The patient describes having few moles overall; the patient says their skin tans without first burning:
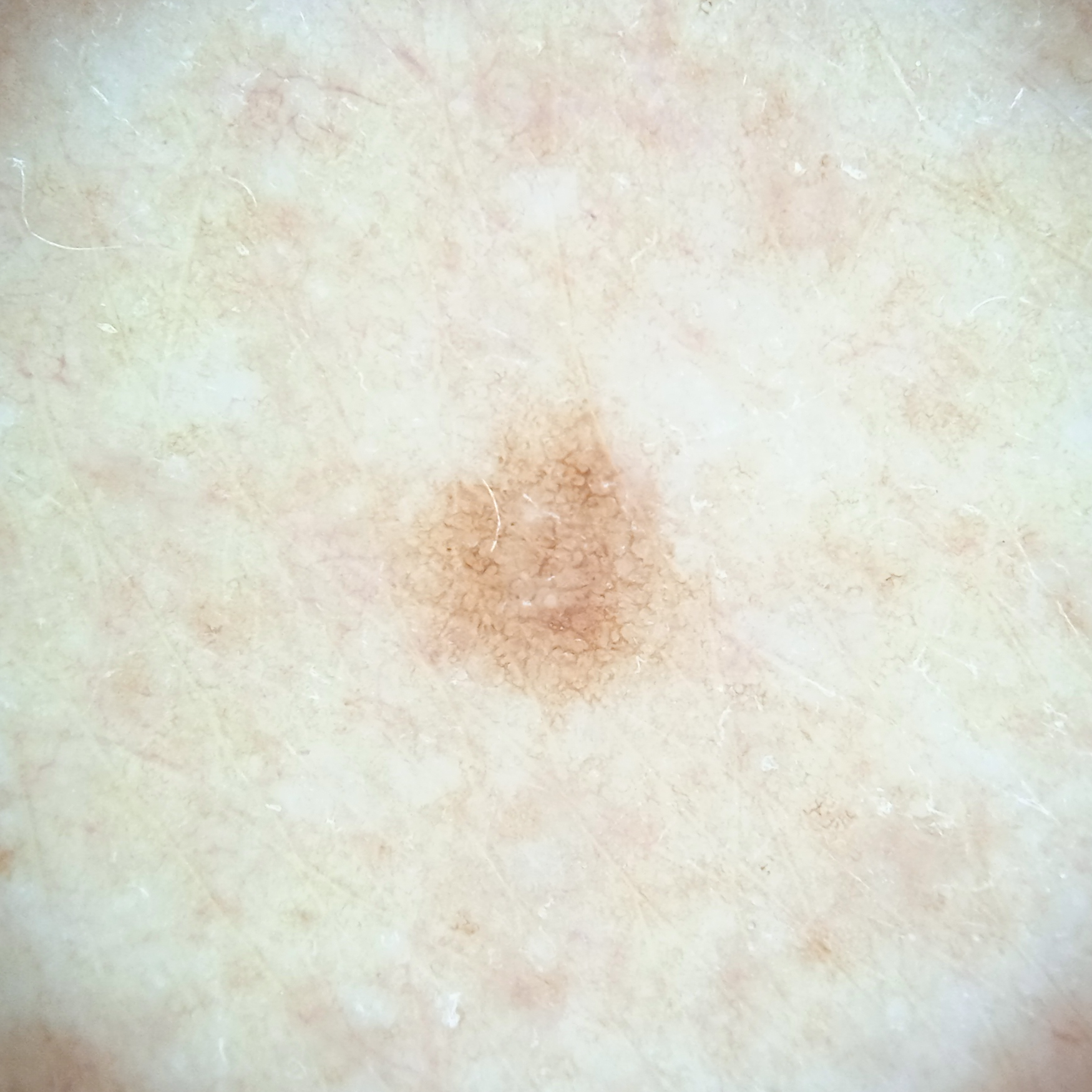Findings:
- body site: an arm
- size: 2.8 mm
- assessment: melanocytic nevus (dermatologist consensus)